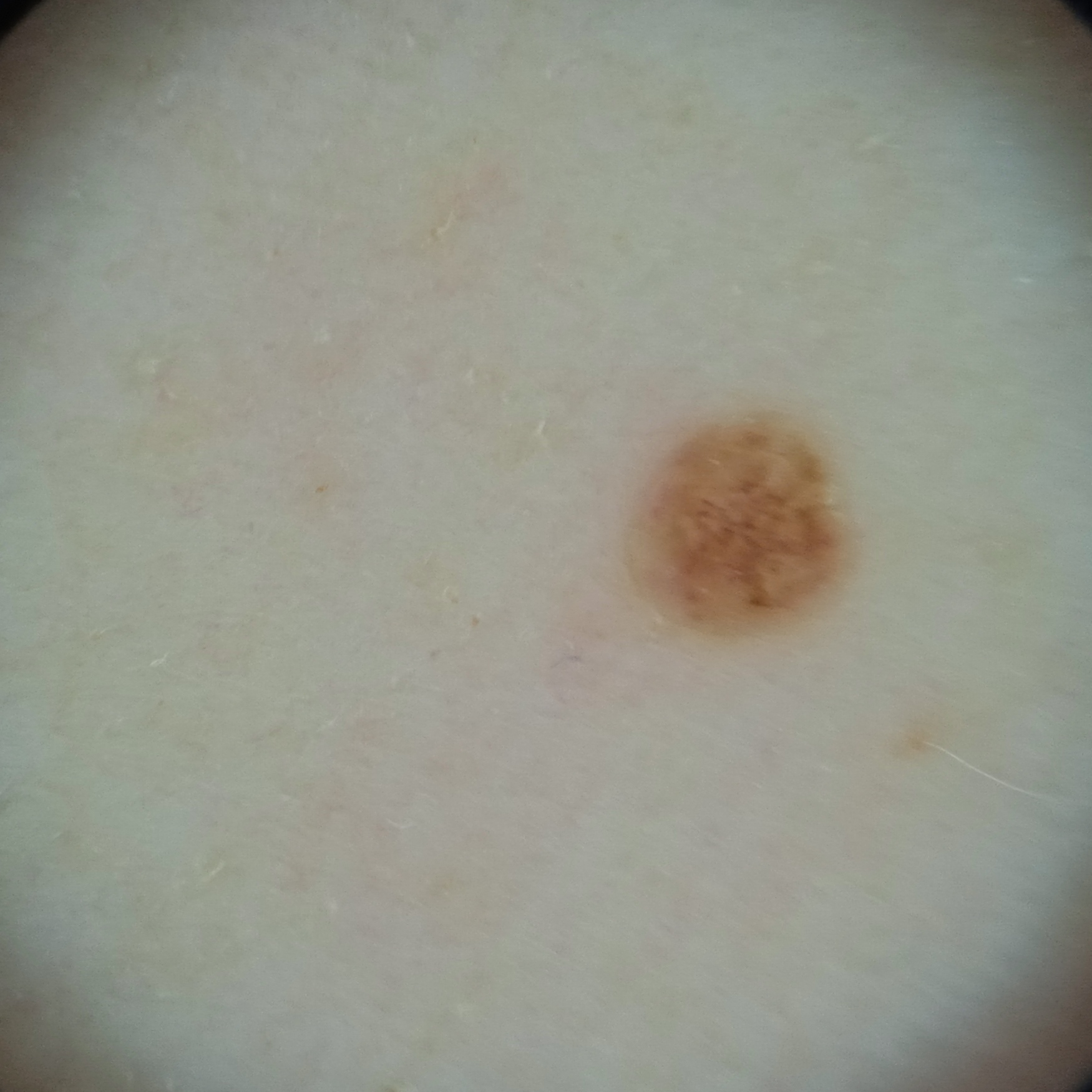A female patient age 50.
Imaged for a research study, with no referral diagnosis recorded.
The lesion involves the back.
Measuring roughly 2.2 mm.
The four-dermatologist consensus diagnosis was a melanocytic nevus.